A dermoscopic image of a skin lesion:
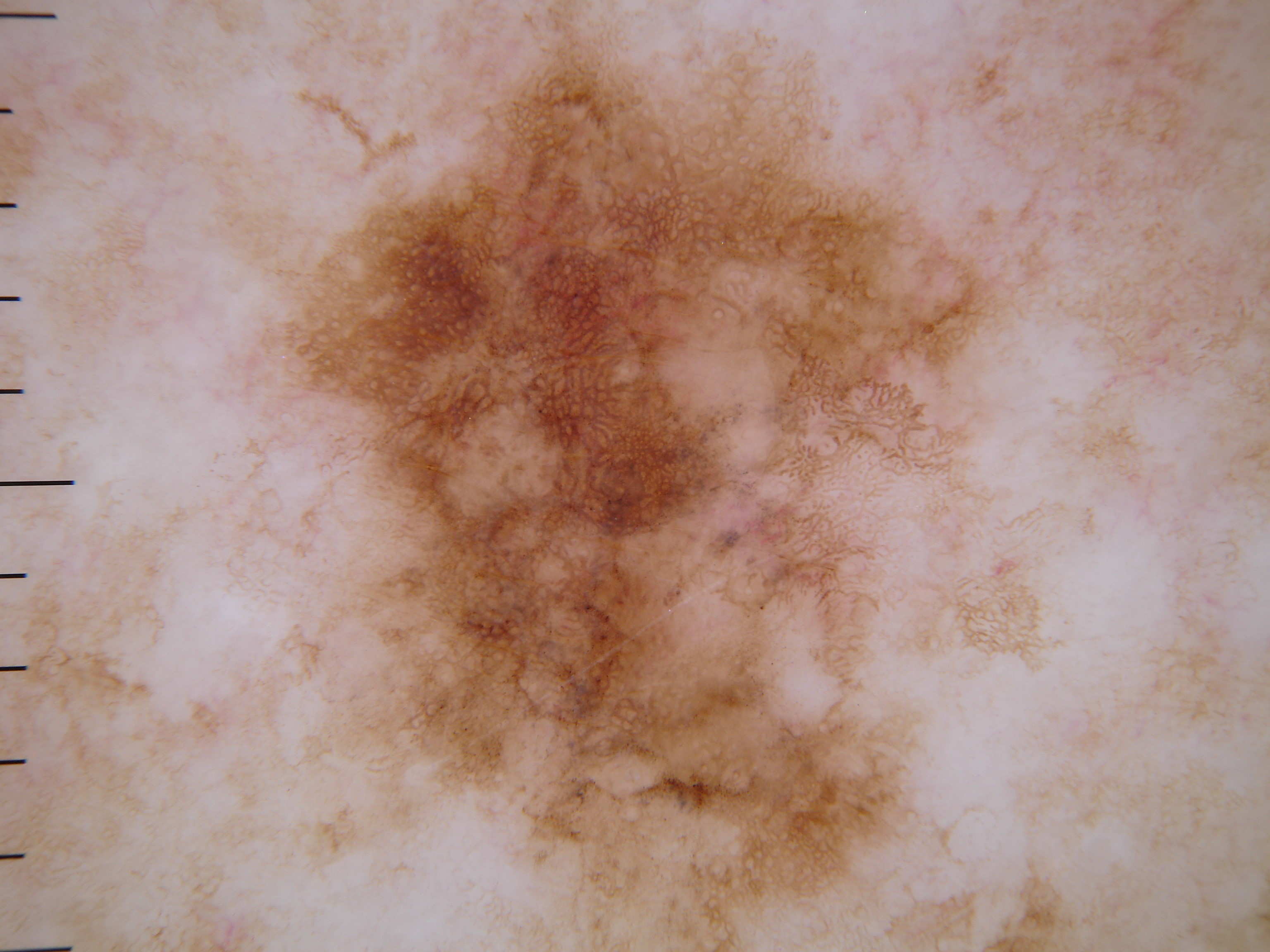lesion bbox = <box>283, 8, 1094, 942</box>
dermoscopic features = globules and pigment network; absent: negative network, streaks, and milia-like cysts
impression = a melanoma